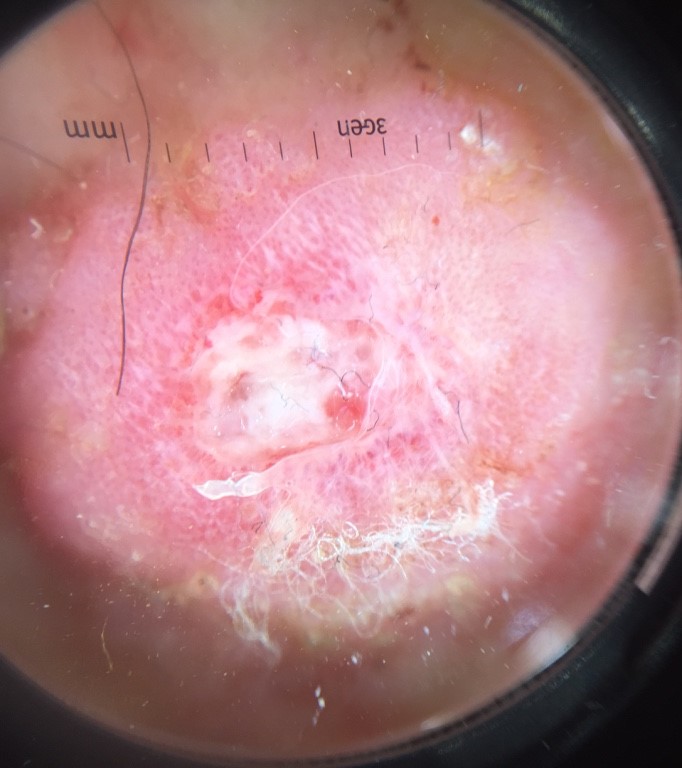Q: What is the imaging modality?
A: dermoscopy
Q: How is the lesion classified?
A: keratinocytic
Q: What is this lesion?
A: squamous cell carcinoma (biopsy-proven)